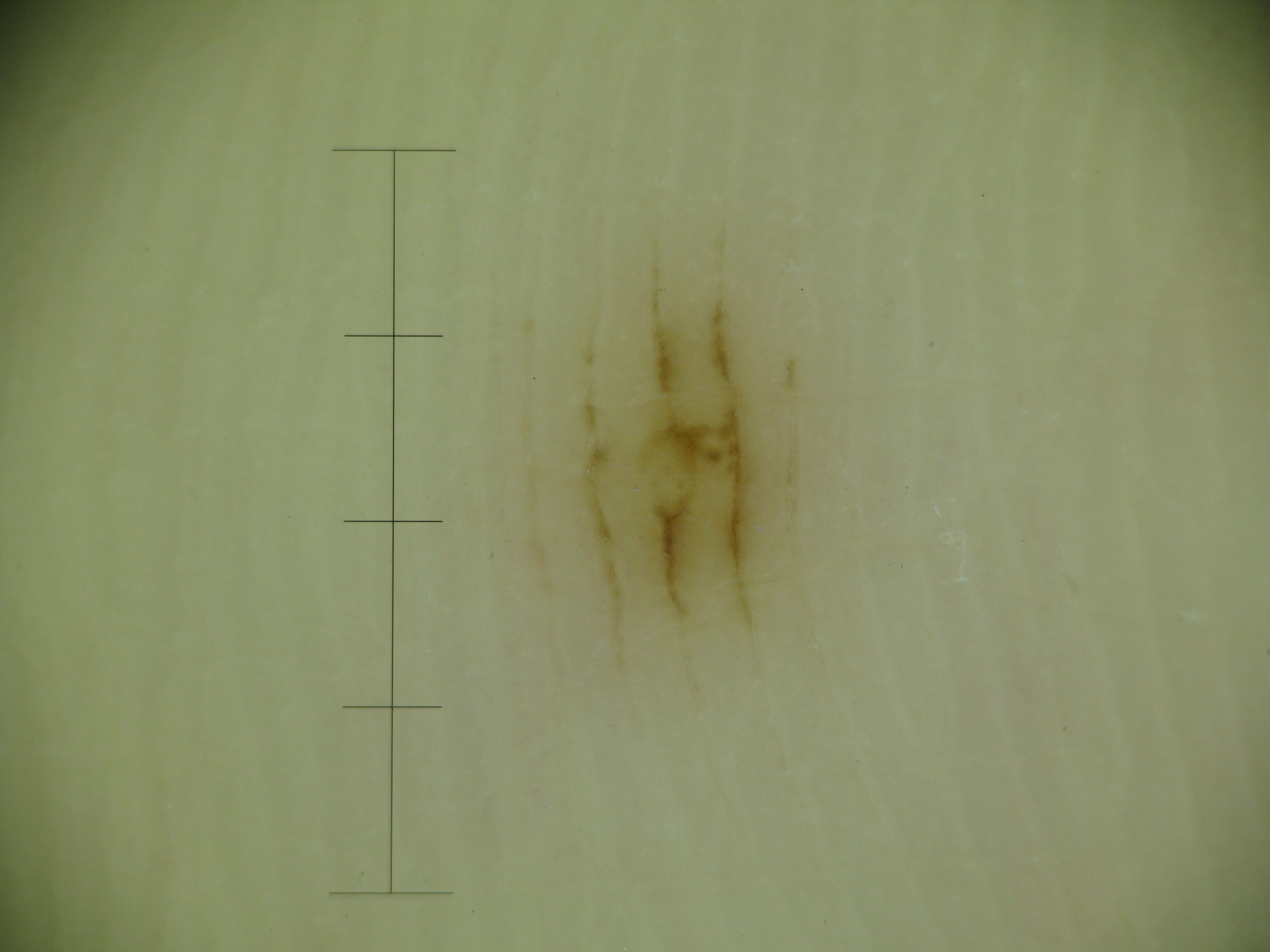Consistent with an acral junctional nevus.